This is a dermoscopic photograph of a skin lesion.
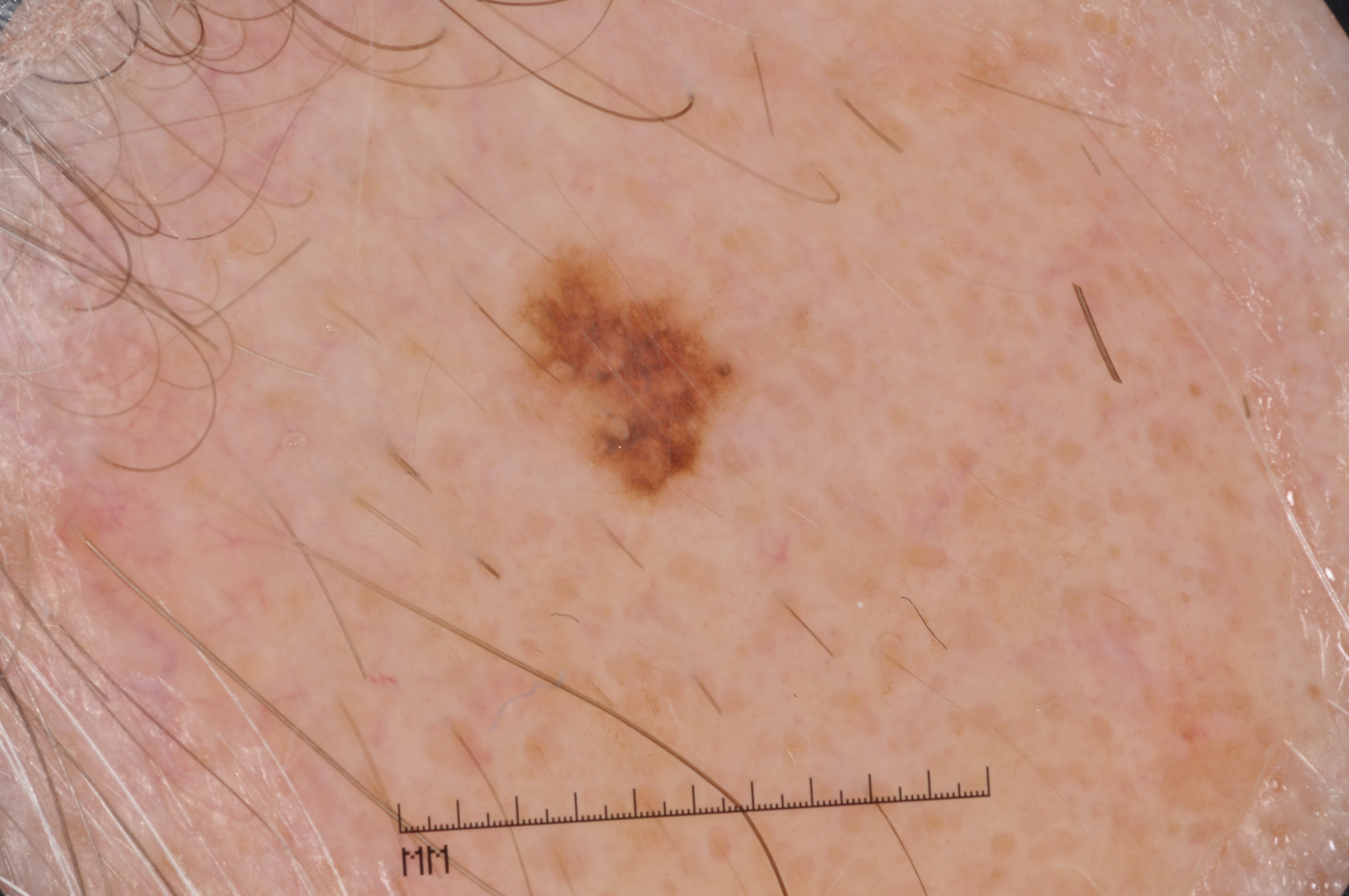dermoscopic findings = pigment network; absent: milia-like cysts, negative network, and streaks | lesion location = left=517, top=252, right=738, bottom=490 | diagnostic label = a melanoma.